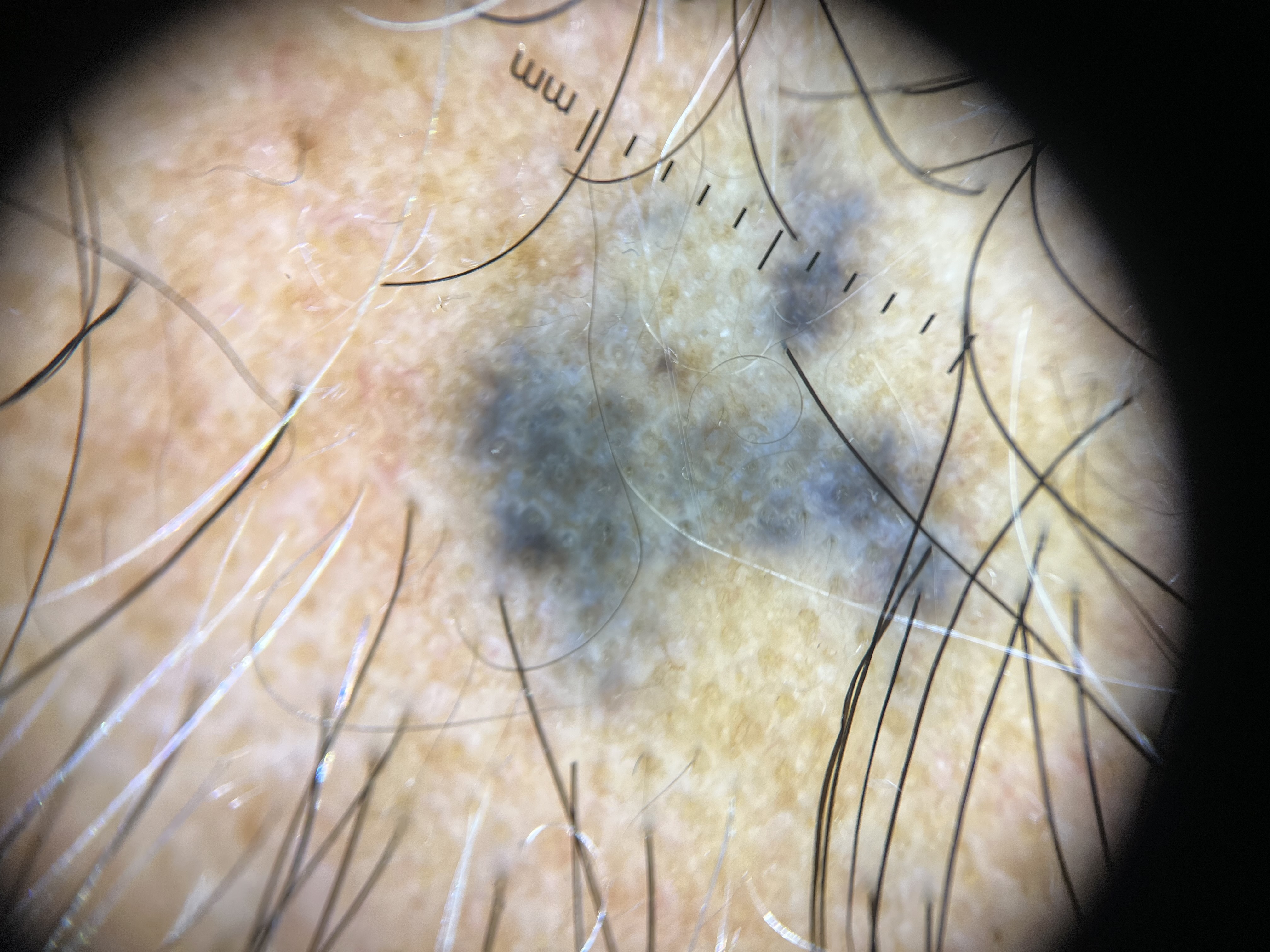label: blue nevus (expert consensus).